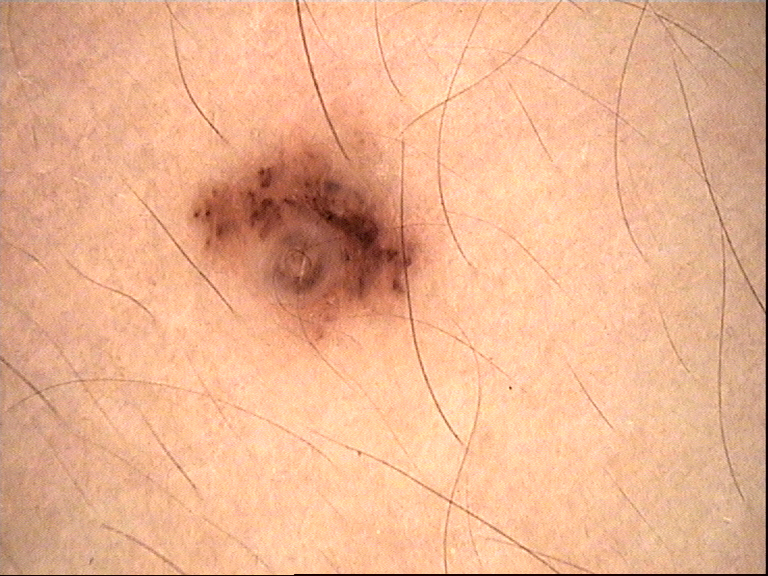– lesion type — banal
– diagnostic label — compound nevus (expert consensus)